A skin lesion imaged with a dermatoscope:
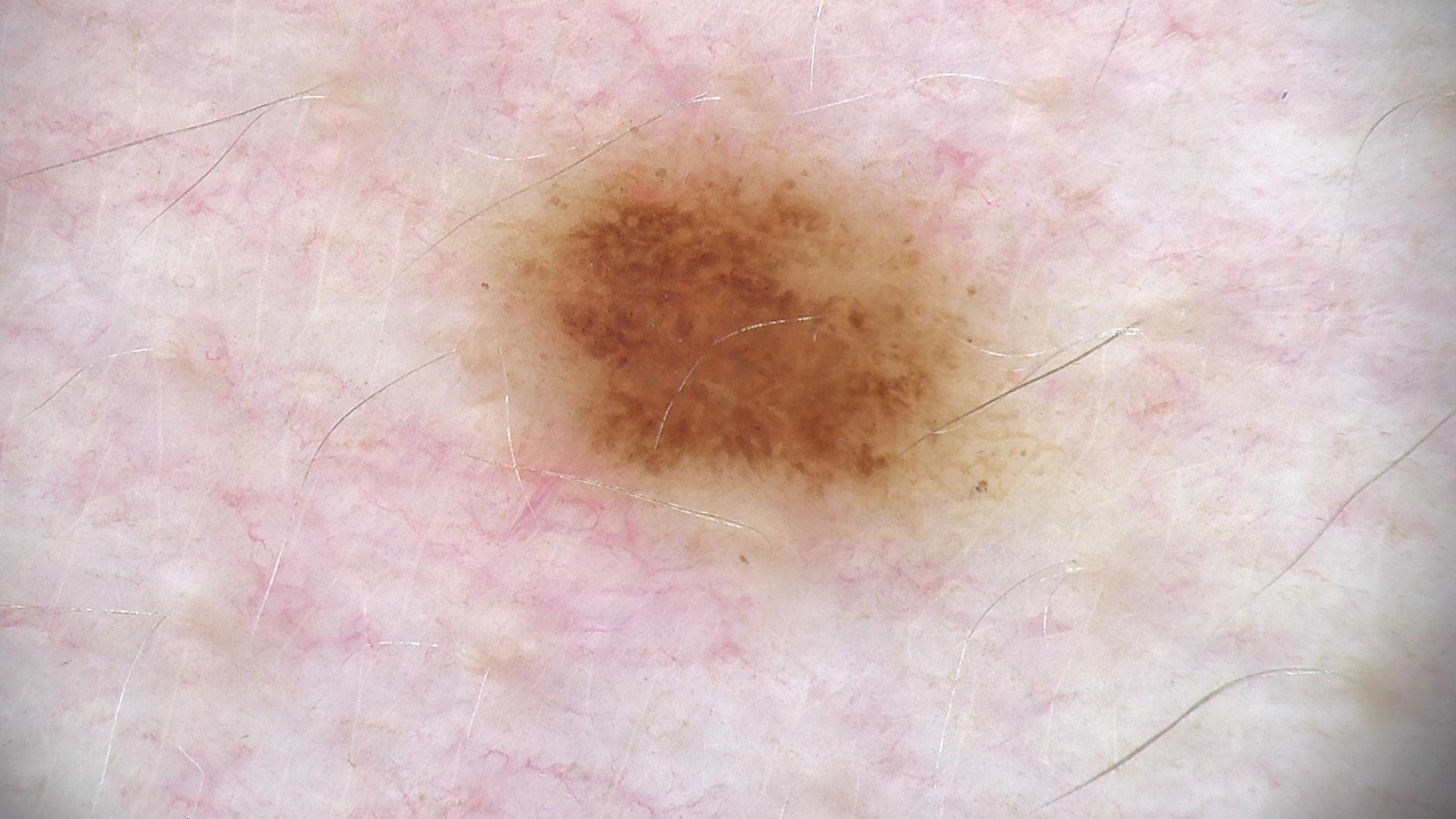Consistent with a dysplastic junctional nevus.